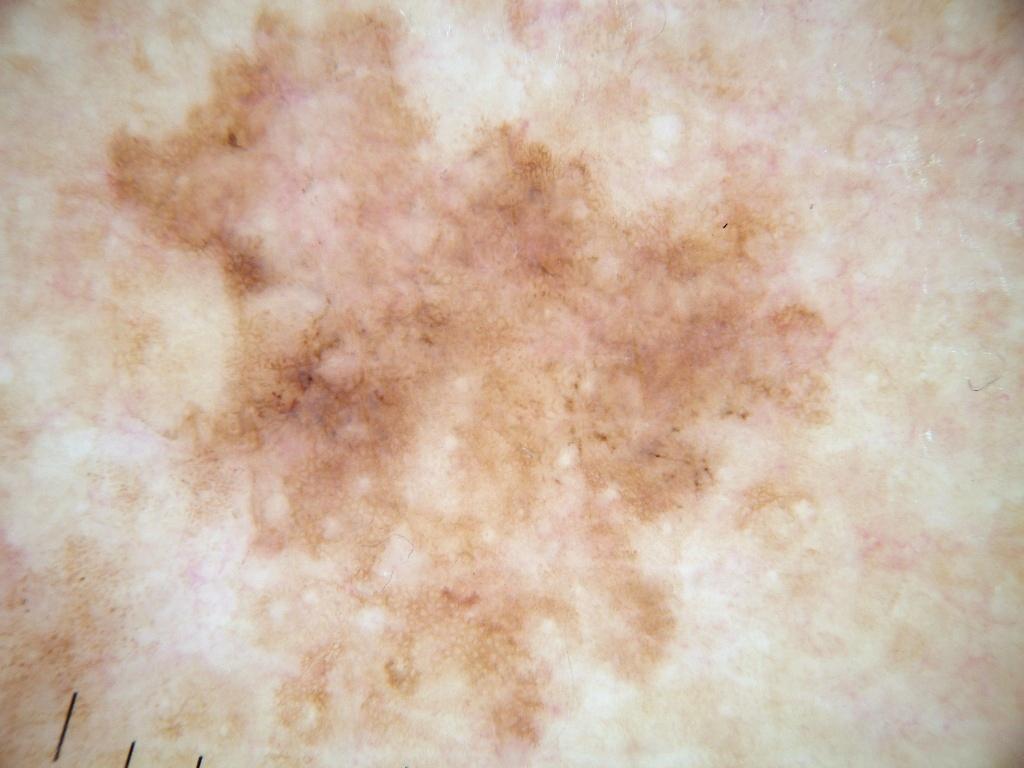Case summary:
A dermoscopic image of a skin lesion. A female subject, aged 63-67. Dermoscopically, the lesion shows pigment network; no globules, streaks, milia-like cysts, or negative network. As (left, top, right, bottom), the lesion occupies the region (81, 4, 848, 765).
Conclusion:
Confirmed on histopathology as a melanoma, a malignant lesion.